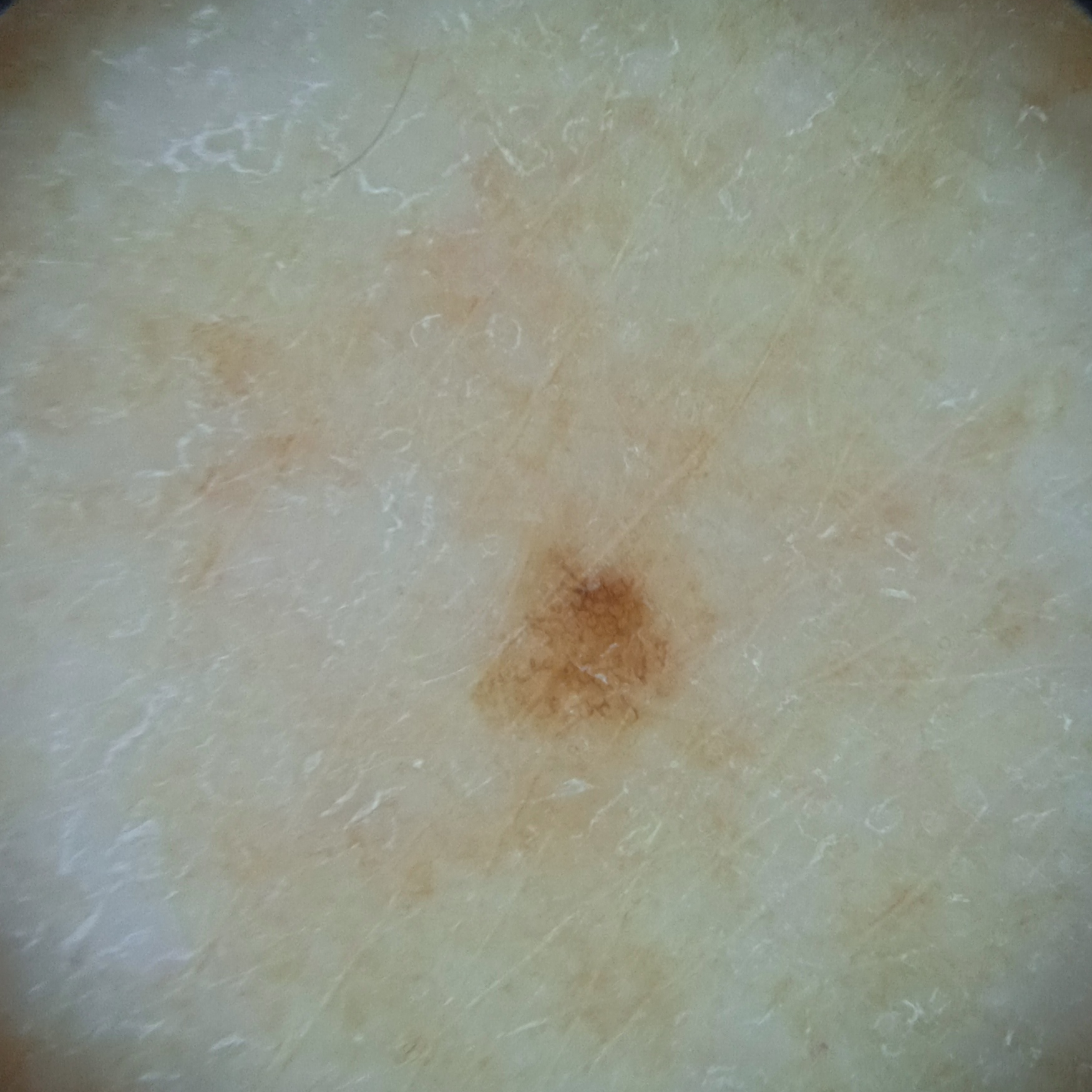<lesion>
  <sun_reaction>skin tans without first burning</sun_reaction>
  <image>dermoscopic image</image>
  <referral>research study (no referral diagnosis)</referral>
  <lesion_location>an arm</lesion_location>
  <diagnosis>
    <name>melanocytic nevus</name>
    <malignancy>benign</malignancy>
  </diagnosis>
</lesion>